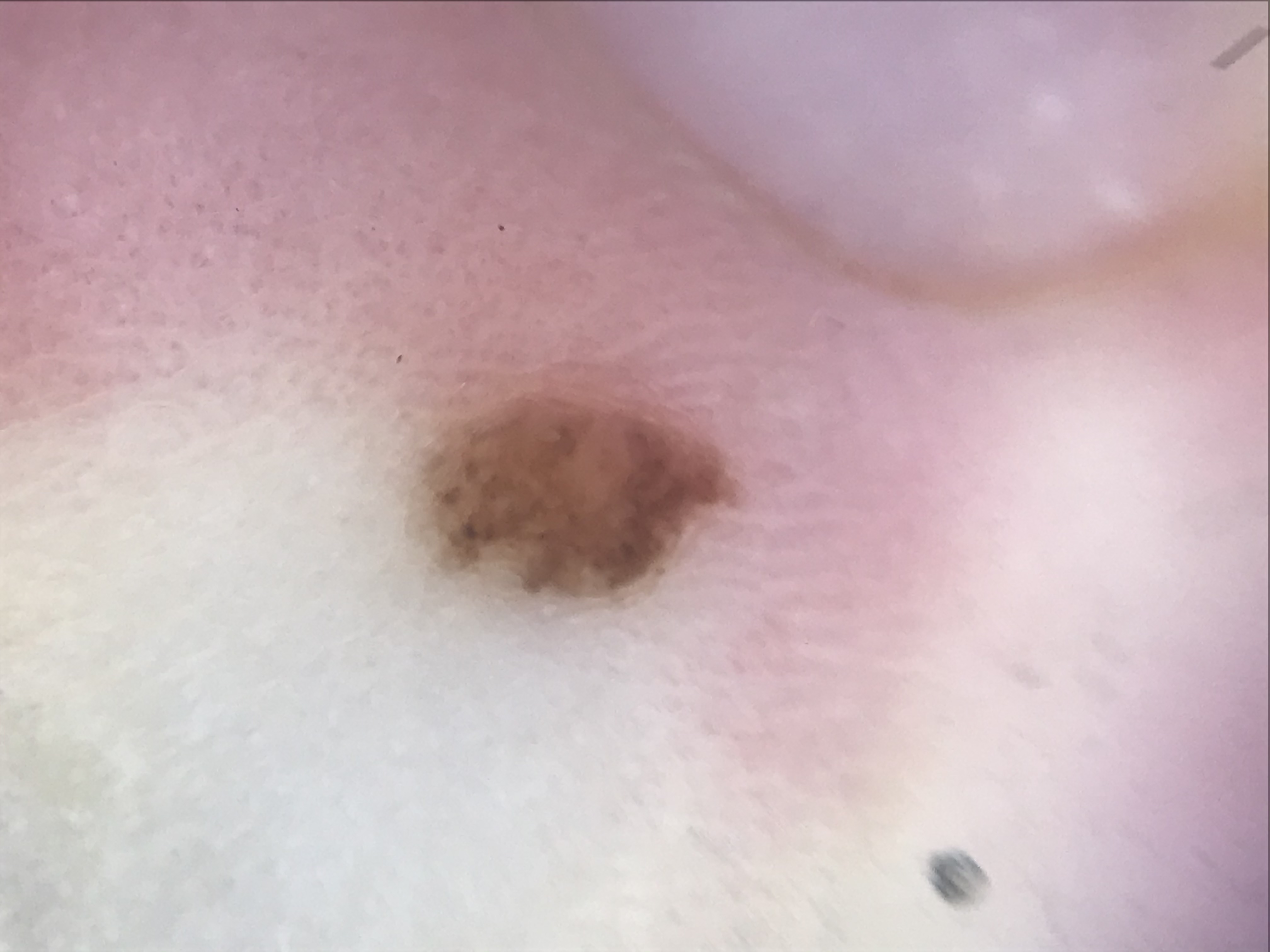A skin lesion imaged with a dermatoscope. The architecture is that of a banal lesion. Consistent with an acral compound nevus.